A dermatoscopic image of a skin lesion; a male patient, approximately 10 years of age:
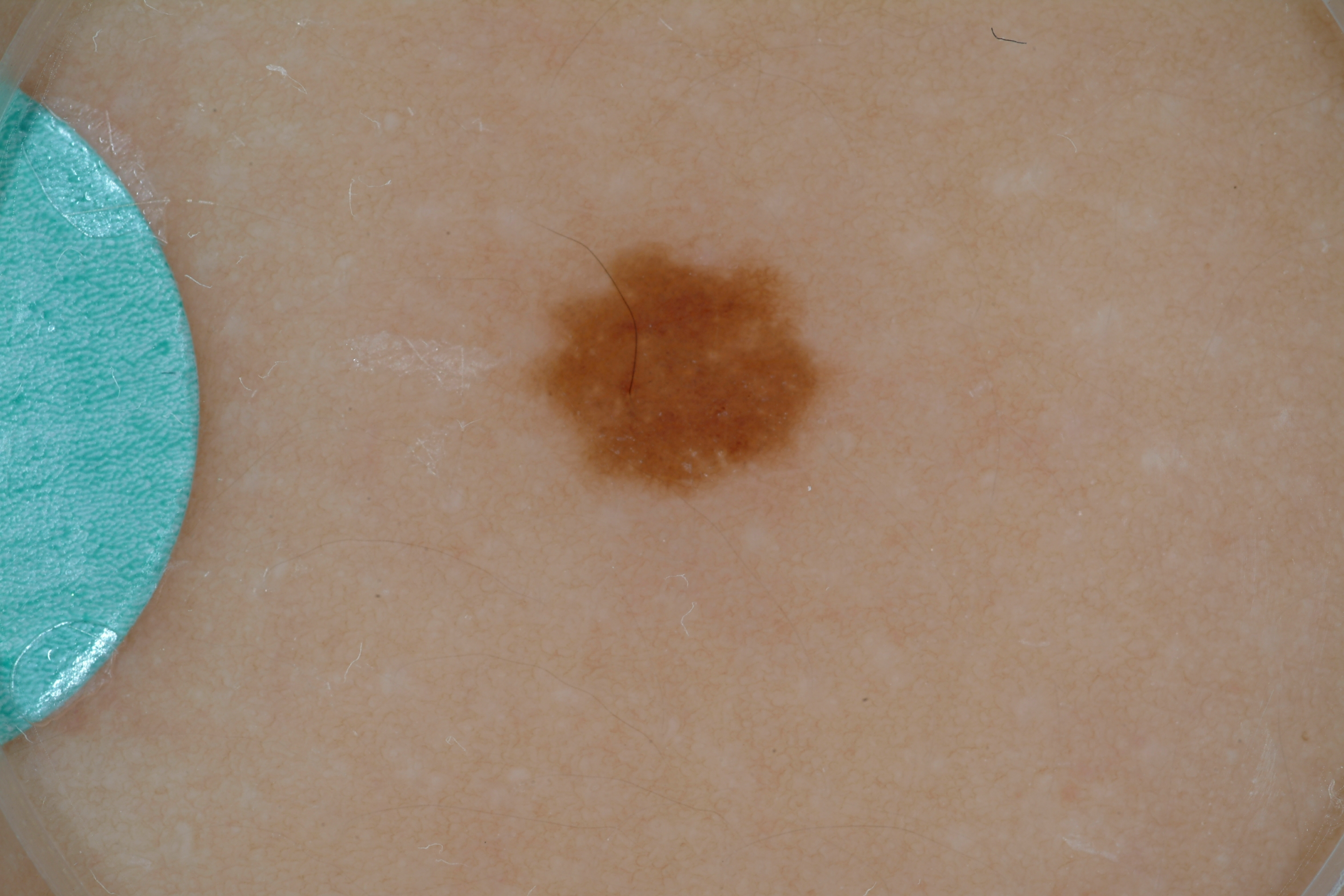The lesion is located at left=499, top=227, right=850, bottom=506. Dermoscopy demonstrates pigment network; no globules, streaks, negative network, or milia-like cysts. The lesion takes up about 6% of the image. Consistent with a melanocytic nevus, a benign lesion.